A dermatoscopic image of a skin lesion: 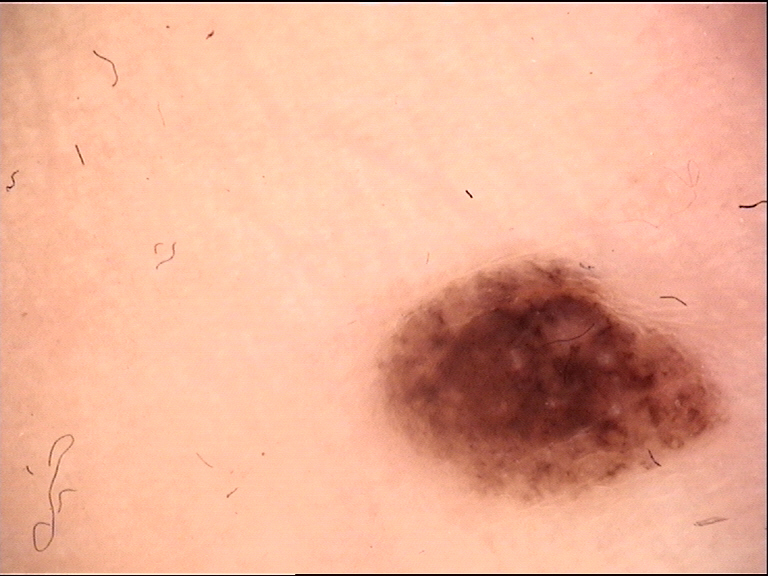Q: What kind of lesion is this?
A: banal
Q: What was the diagnostic impression?
A: compound nevus (expert consensus)